The lesion involves the sole of the foot, the photo was captured at a distance.
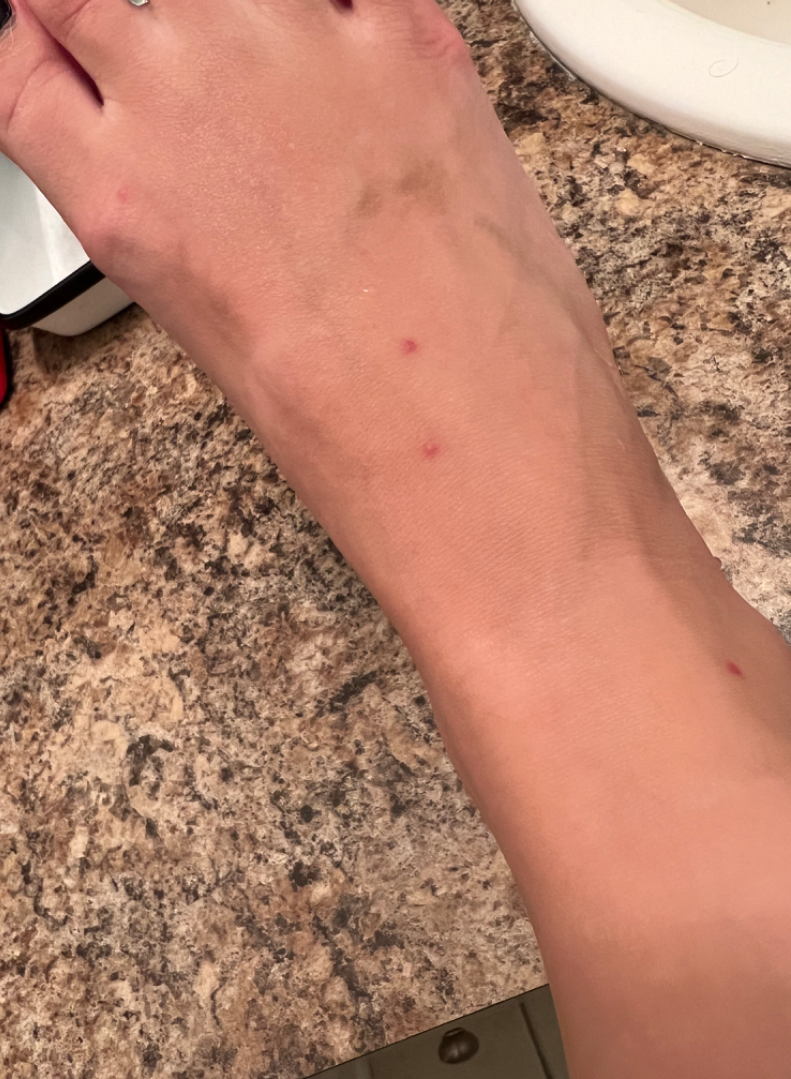Review:
Most likely Insect Bite; the differential also includes Dermatofibroma; a remote consideration is Skin cancer.